The subject is a female aged 53-57 · dermoscopy of a skin lesion:
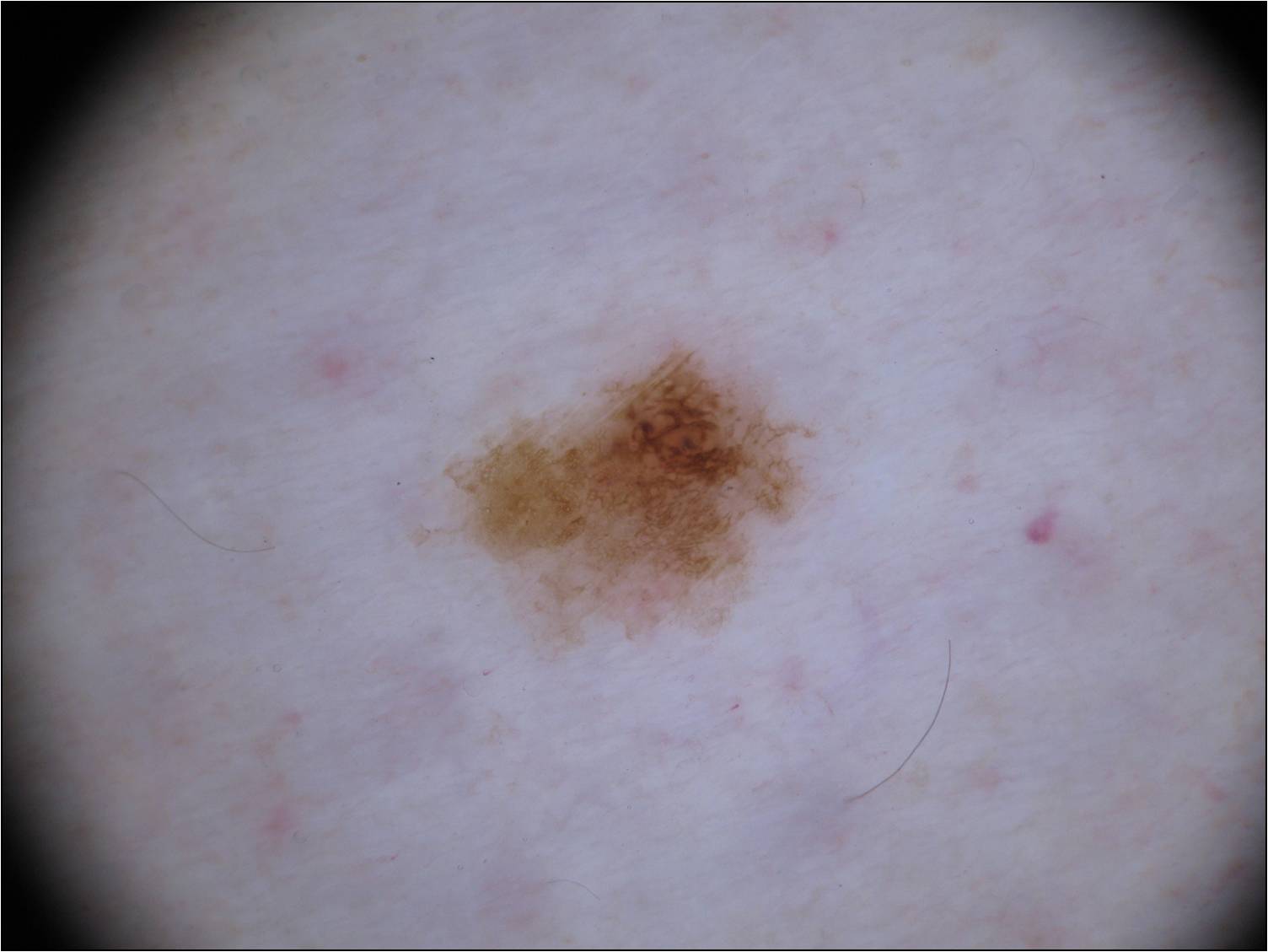dermoscopic features = pigment network; absent: milia-like cysts, negative network, streaks, and globules
location = box(411, 339, 811, 644)
extent = small
impression = a melanocytic nevus